Skin tone: Fitzpatrick II; lay reviewers estimated MST 2 or 3 · the photograph is a close-up of the affected area: 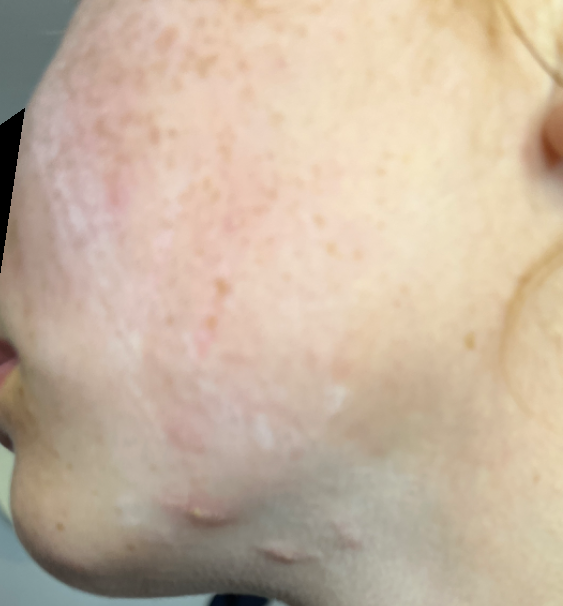The condition could not be reliably identified from the image.